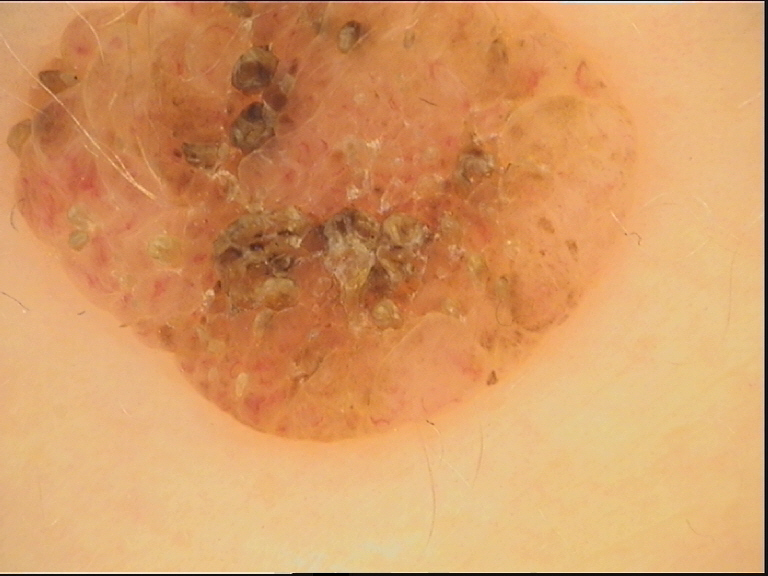Diagnosed as a dermal nevus.